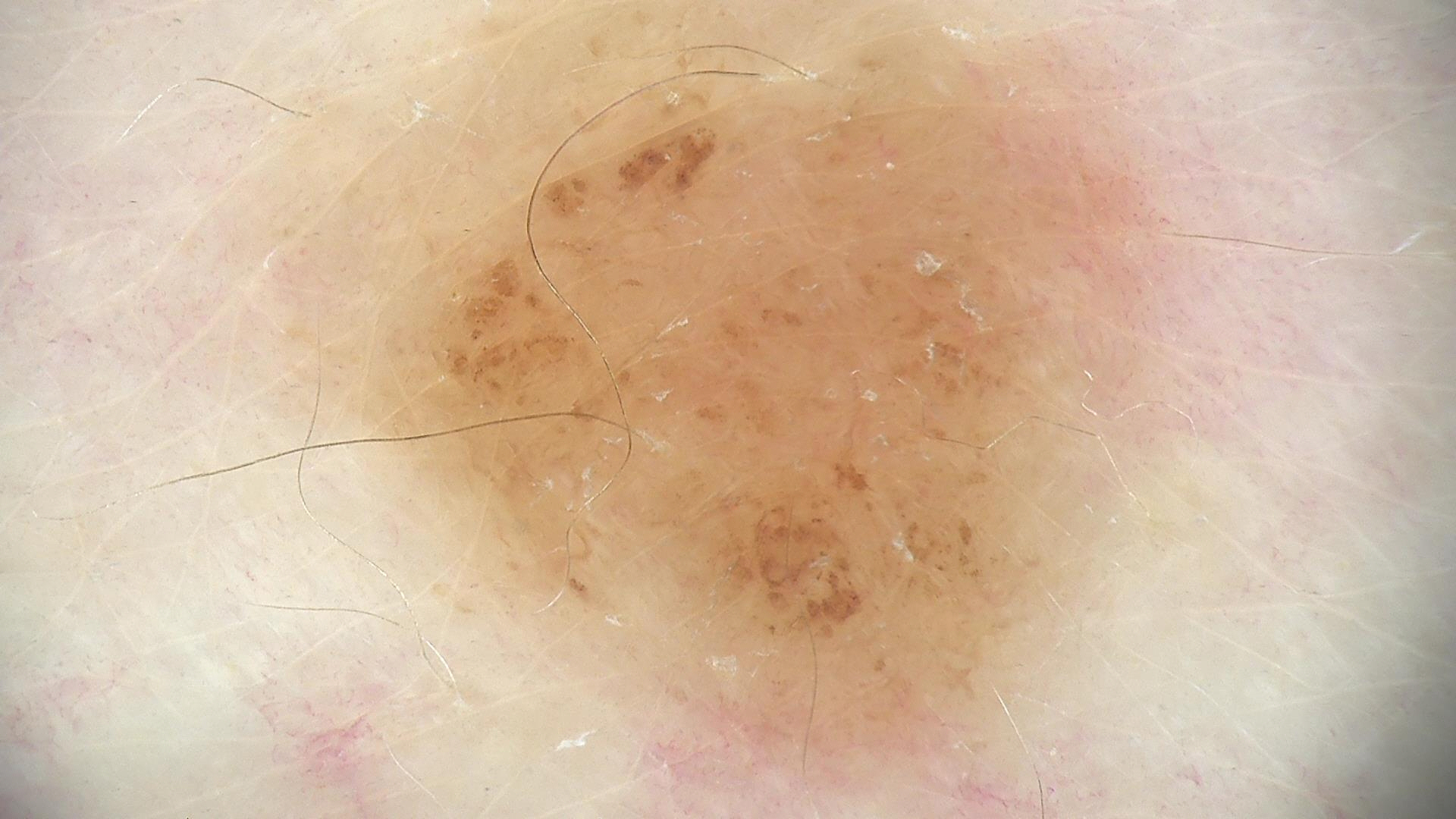Diagnosed as a dysplastic junctional nevus.